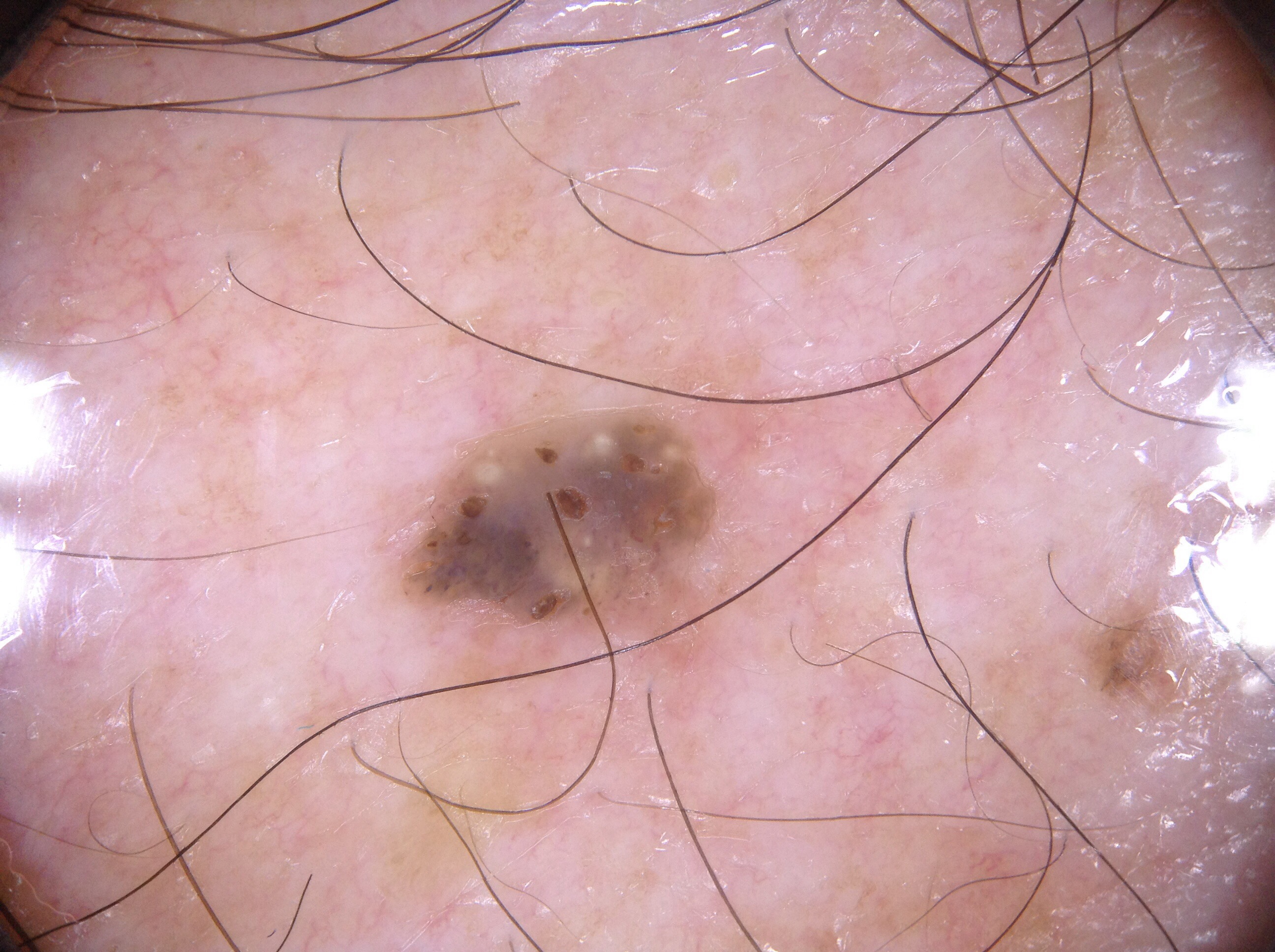Case summary:
* image: dermoscopic image
* patient: male, about 70 years old
* lesion location: box(409, 424, 717, 625)
* dermoscopic findings: milia-like cysts
* diagnosis: a seborrheic keratosis